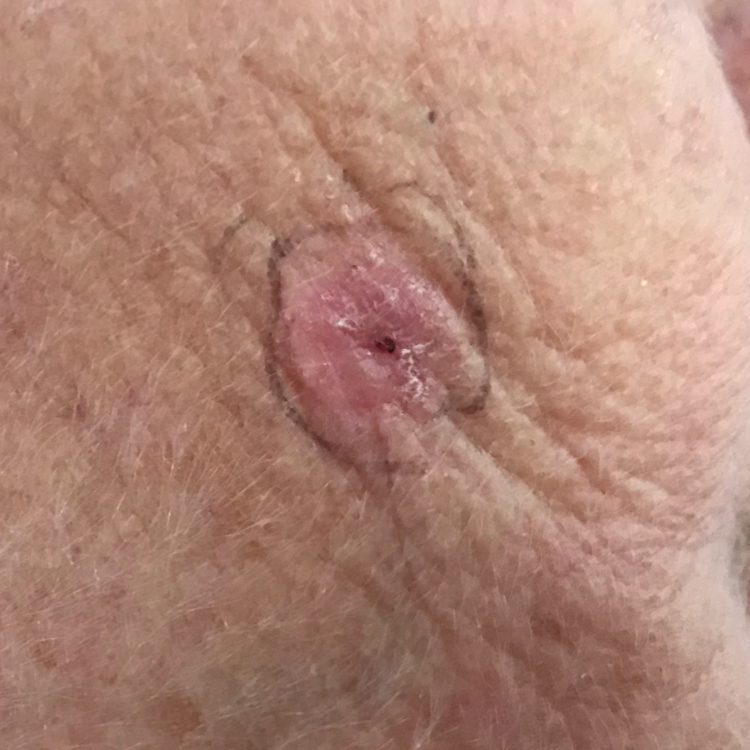<lesion>
<image>smartphone clinical photo</image>
<patient>
<age>62</age>
<gender>female</gender>
</patient>
<lesion_location>the face</lesion_location>
<symptoms>
<present>elevation, growth, itching</present>
</symptoms>
<diagnosis>
<name>basal cell carcinoma</name>
<code>BCC</code>
<malignancy>malignant</malignancy>
<confirmation>histopathology</confirmation>
</diagnosis>
</lesion>